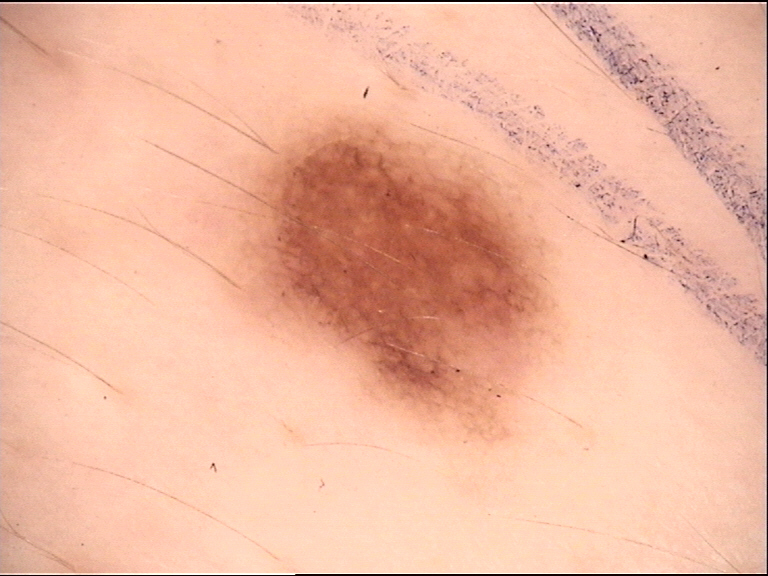| feature | finding |
|---|---|
| diagnostic label | dysplastic junctional nevus (expert consensus) |